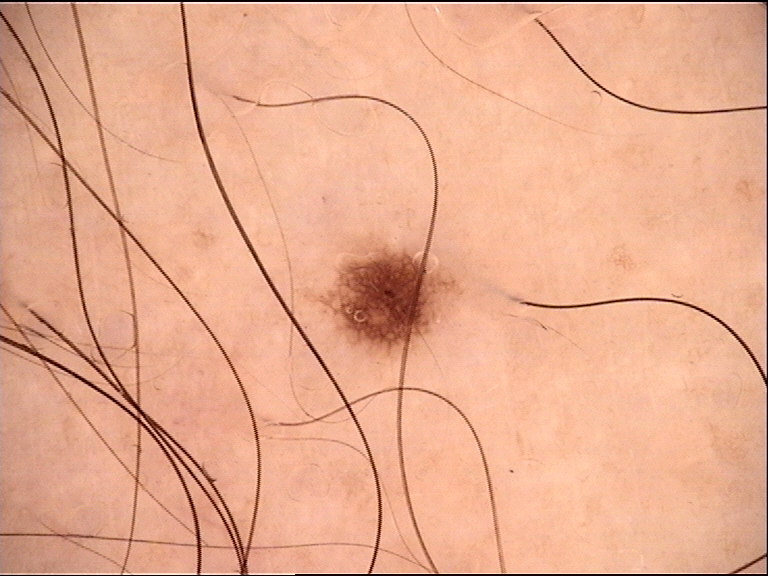<lesion>
  <diagnosis>
    <name>dysplastic junctional nevus</name>
    <code>jd</code>
    <malignancy>benign</malignancy>
    <super_class>melanocytic</super_class>
    <confirmation>expert consensus</confirmation>
  </diagnosis>
</lesion>